The subject is 50–59, female; the photograph was taken at an angle; the lesion involves the palm, leg and arm — 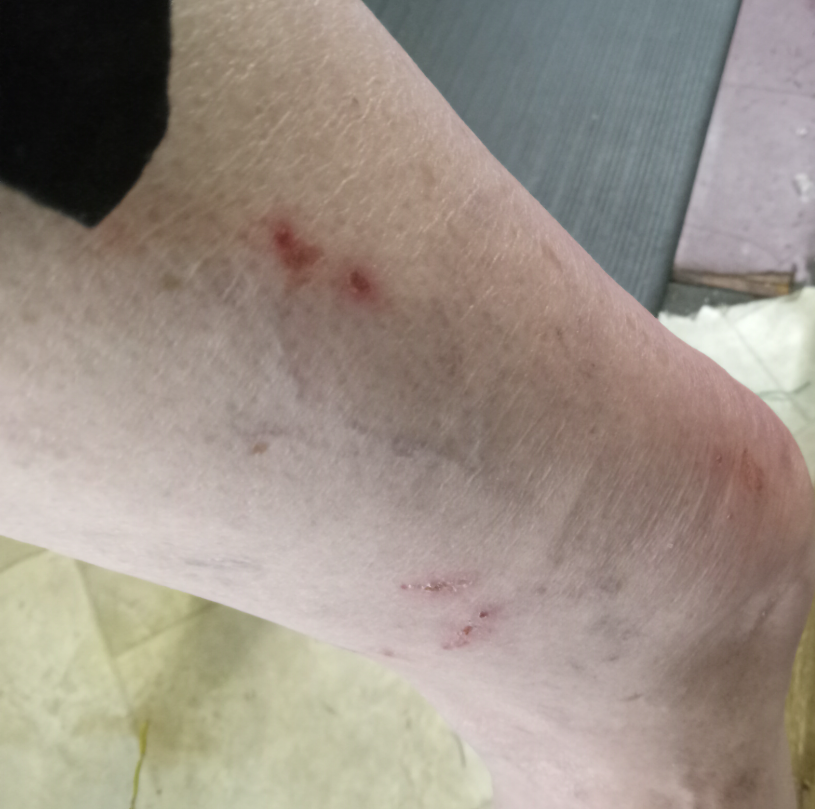skin tone = Fitzpatrick skin type I | lesion symptoms = itching | history = one to four weeks | patient describes the issue as = a rash | differential diagnosis = three dermatologists each reviewed the case: Inflicted skin lesions and Eczema were each considered, in no particular order; less likely is Impetigo; a remote consideration is Localised skin infection.